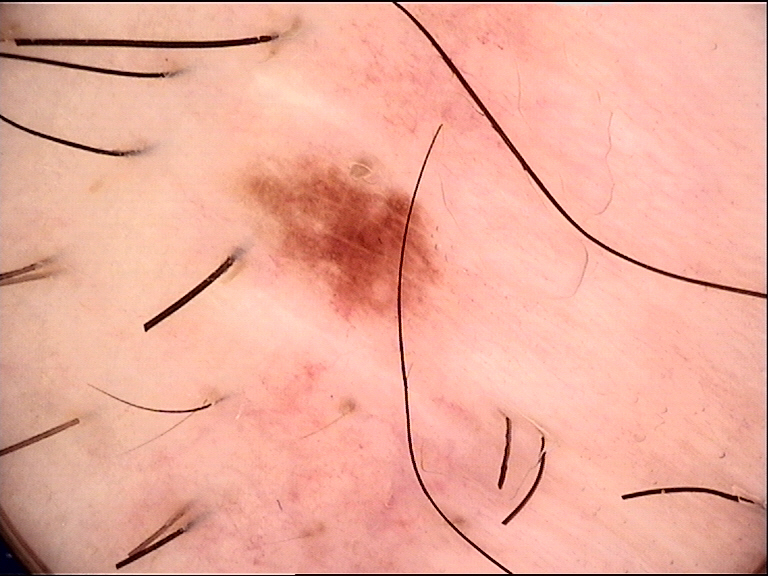Labeled as a dysplastic junctional nevus.